Dermoscopy of a skin lesion — 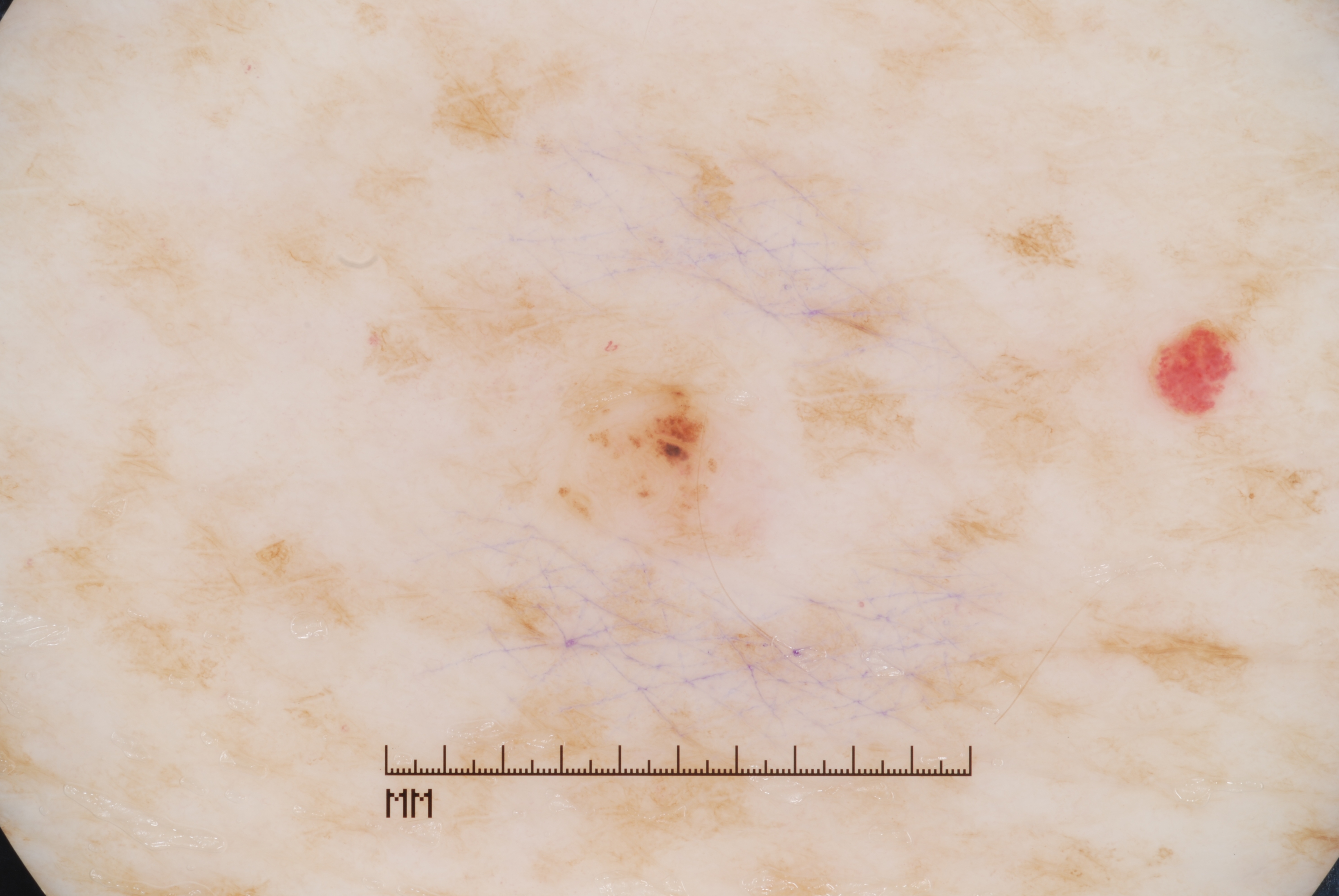Findings:
• absent dermoscopic findings — pigment network, negative network, milia-like cysts, and streaks
• bounding box — bbox=[537, 330, 782, 590]
• extent — small
• assessment — a melanocytic nevus